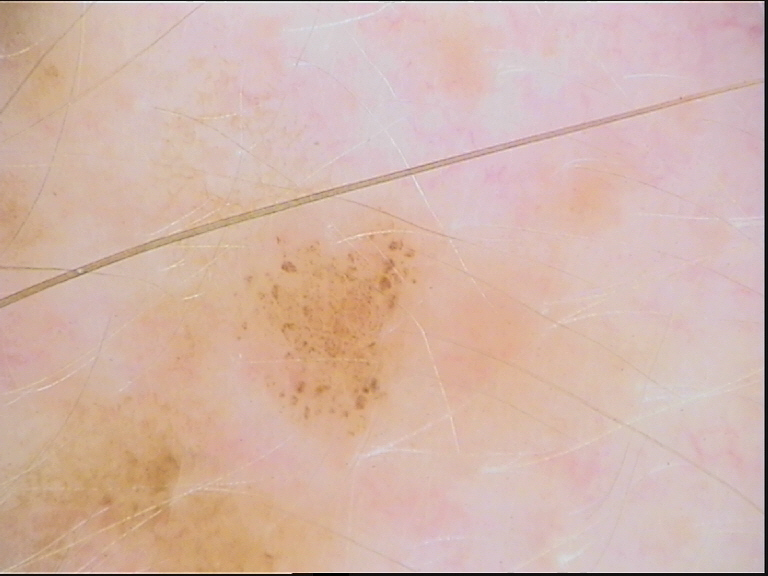diagnostic label = dysplastic junctional nevus (expert consensus)